A clinical photograph showing a skin lesion · a female patient in their late 70s · the patient was assessed as FST III: 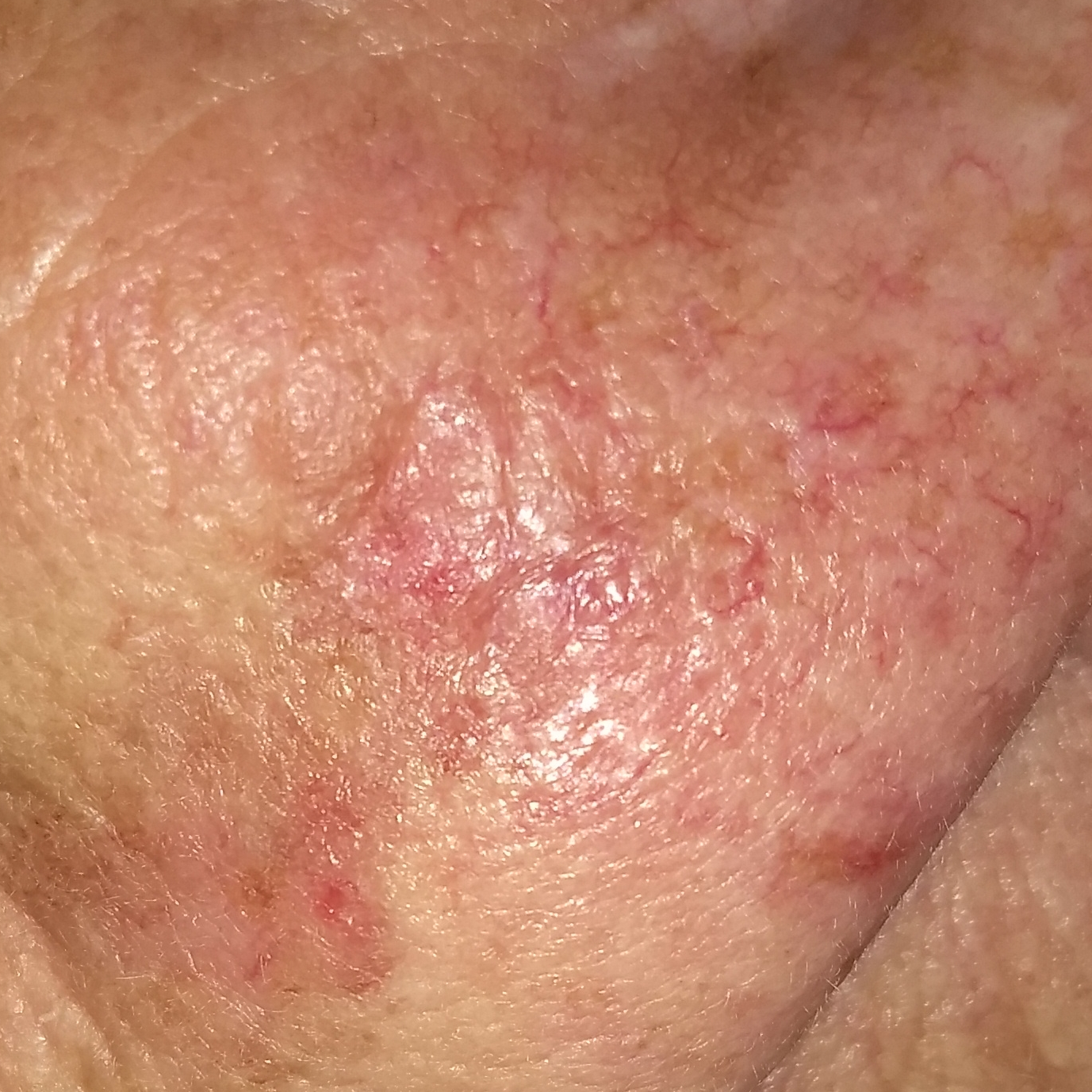Consistent with an actinic keratosis.